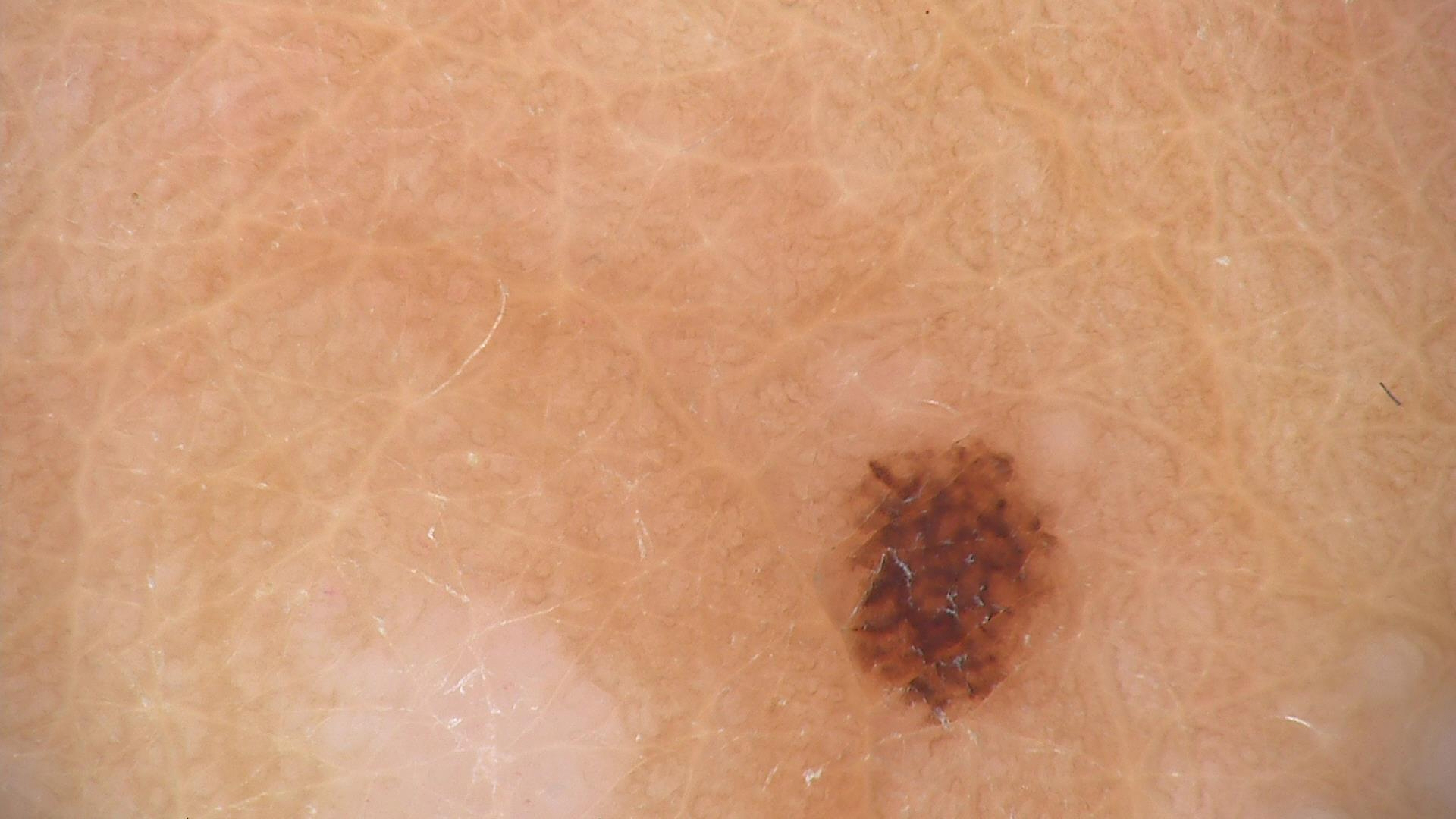* imaging: dermoscopy
* diagnostic label: acral compound nevus (expert consensus)